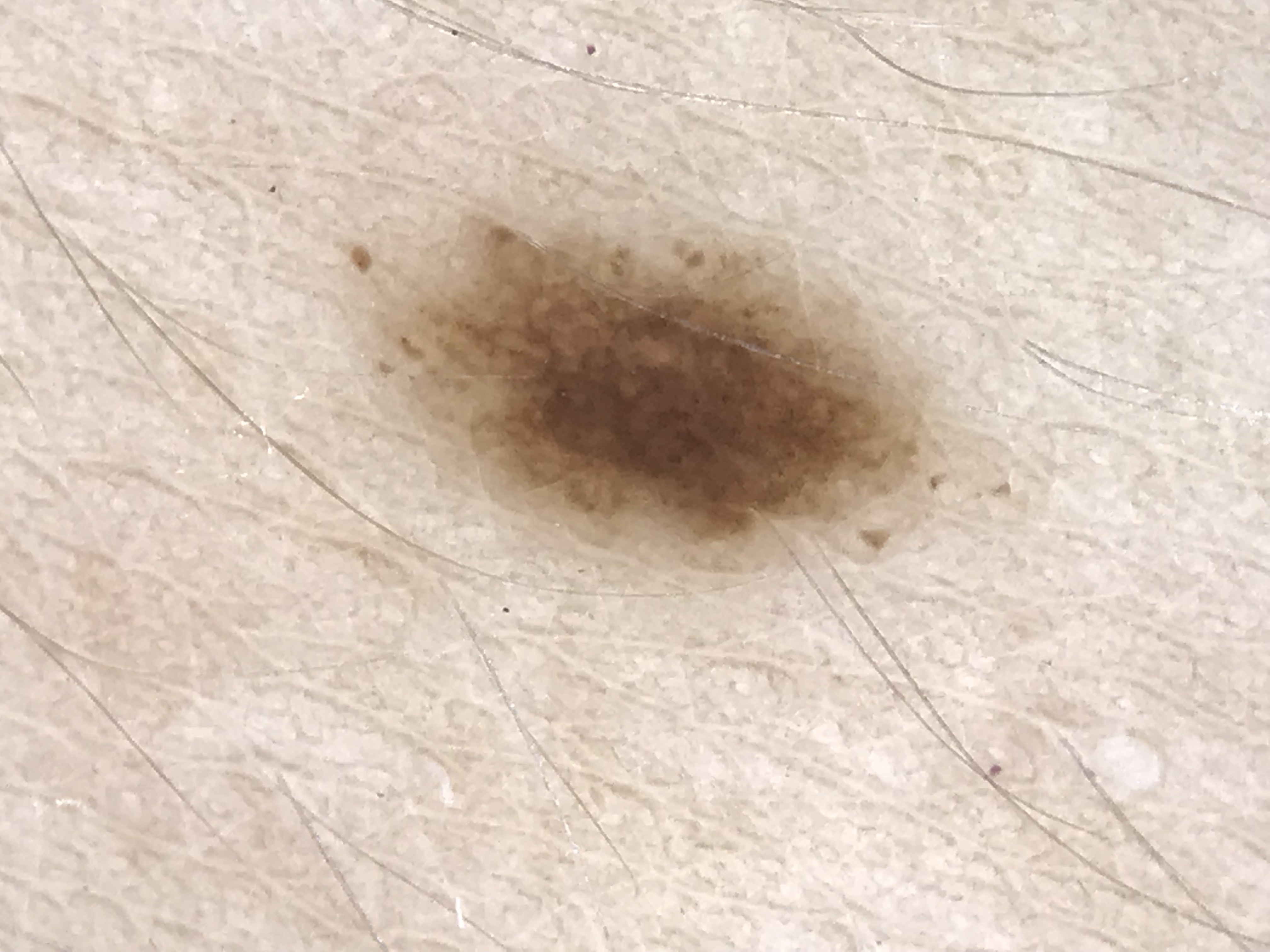Summary:
A skin lesion imaged with a dermatoscope.
Impression:
The diagnostic label was a dysplastic junctional nevus.